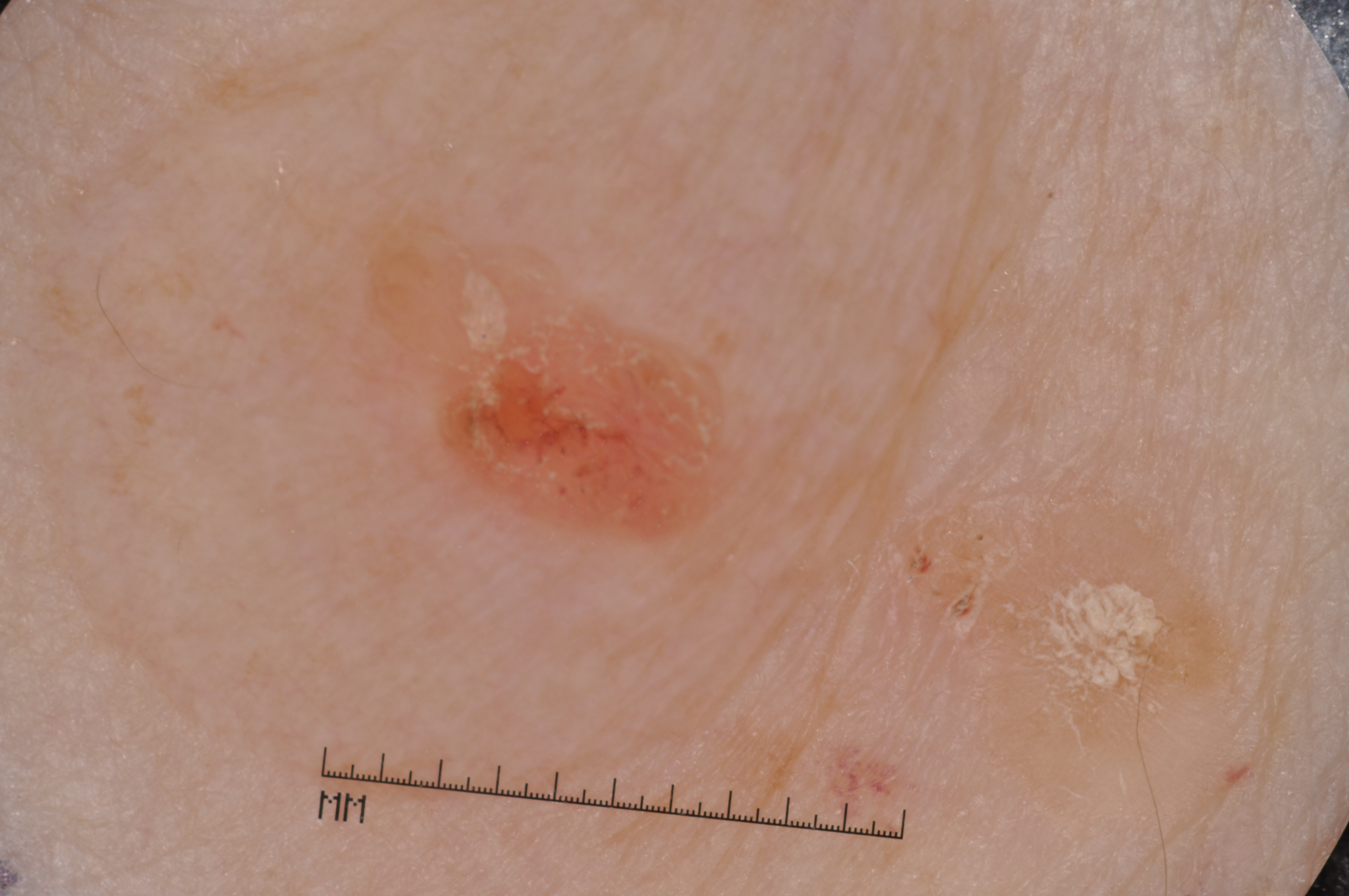Case summary: A female subject aged around 65. A dermoscopy image of a single skin lesion. Dermoscopic examination shows milia-like cysts; no streaks, negative network, or pigment network. The lesion's extent is x1=348, y1=210, x2=769, y2=560. Impression: Consistent with a seborrheic keratosis, a benign lesion.